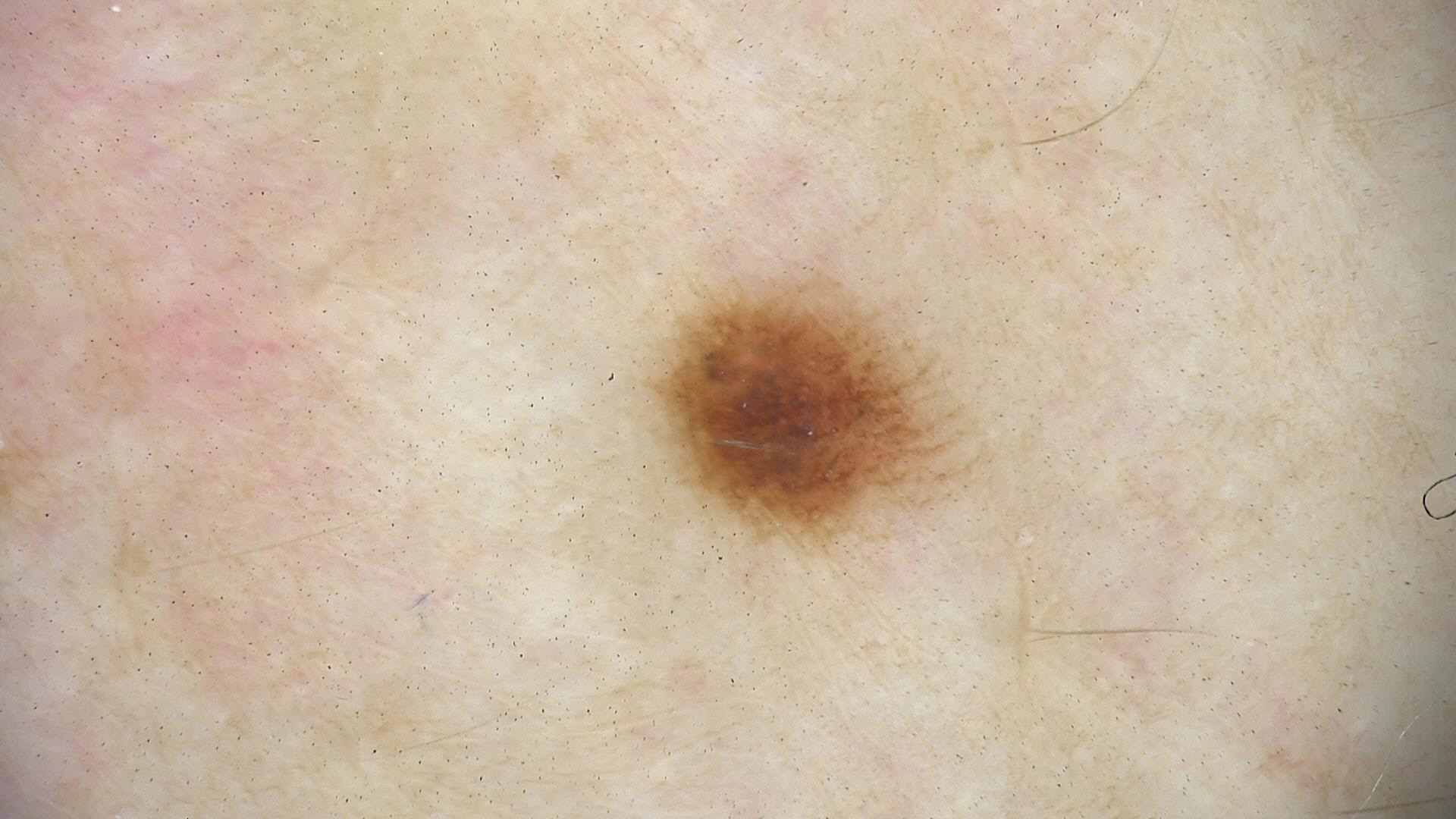A dermoscopic photograph of a skin lesion. Consistent with a dysplastic junctional nevus.